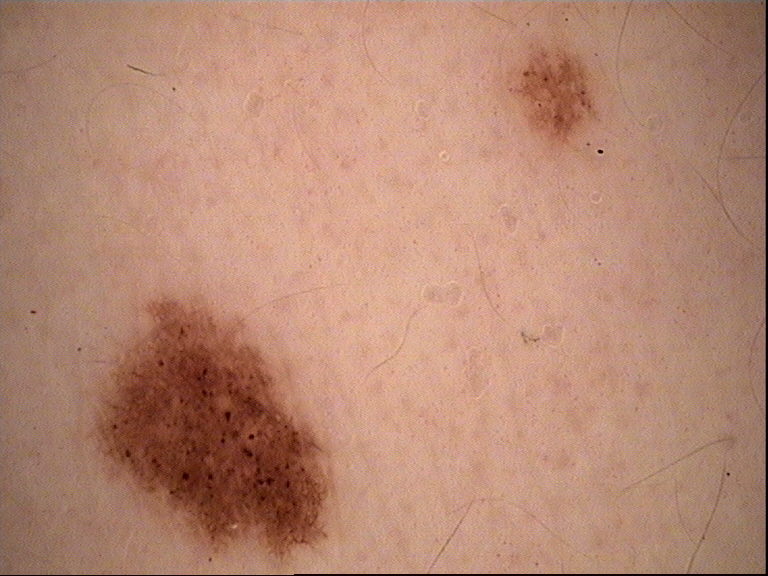The diagnosis was a dysplastic junctional nevus.